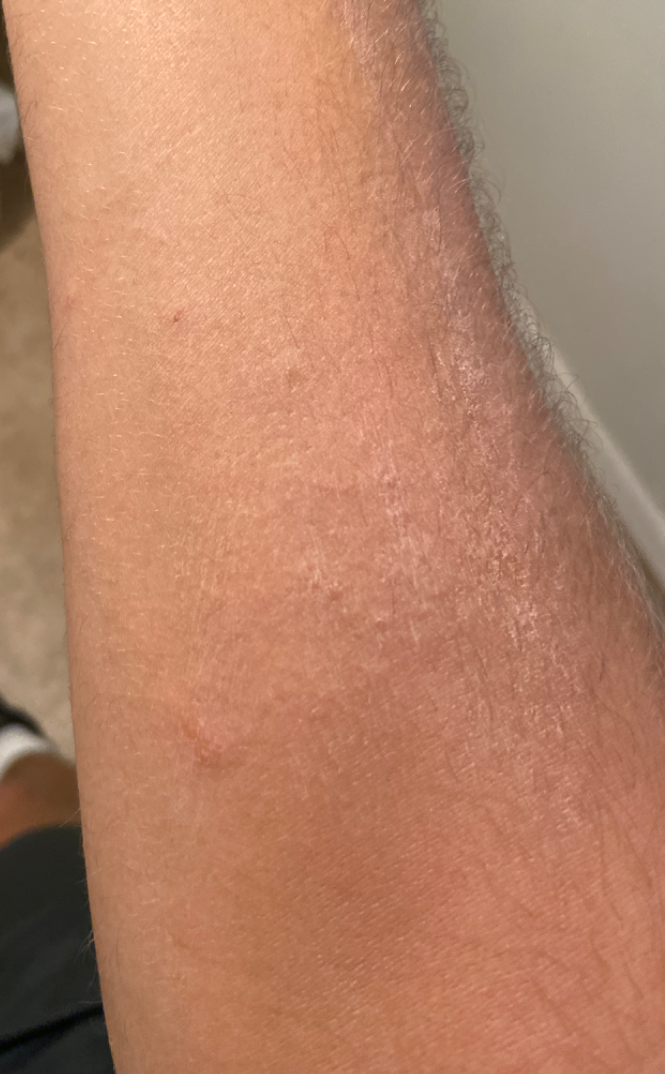Findings:
* location · arm and front of the torso
* texture · raised or bumpy
* skin tone · lay reviewers estimated a Monk skin tone scale of 4
* duration · less than one week
* associated systemic symptoms · none reported
* framing · close-up
* dermatologist impression · Acute and chronic dermatitis (most likely)